Dermoscopy of a skin lesion.
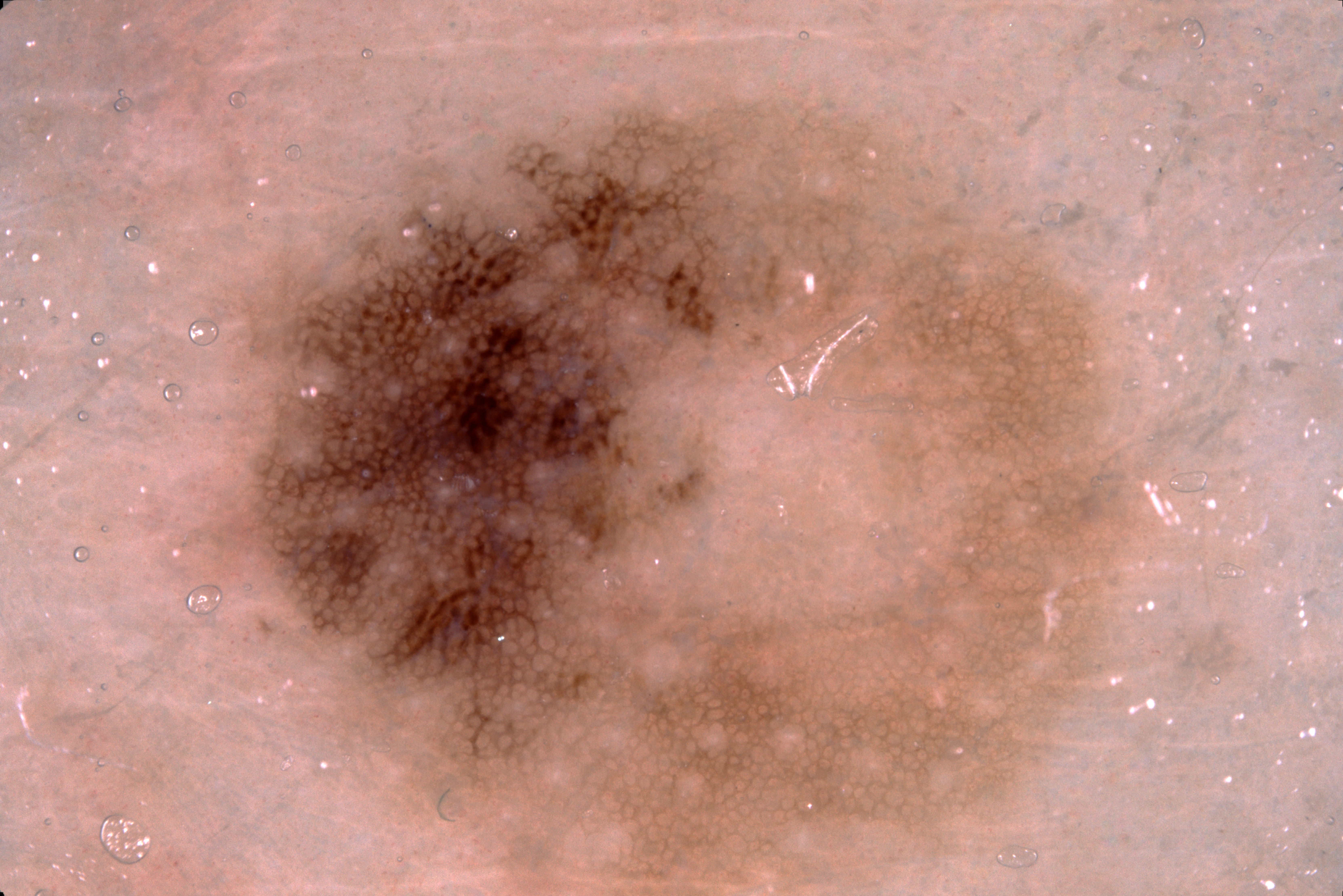Case summary: Dermoscopic review identifies pigment network. The lesion takes up about 51% of the image. In (x1, y1, x2, y2) order, the lesion spans [163,42,1158,895]. The lesion is clipped by the edge of the image. Impression: Expert review diagnosed this as a melanocytic nevus.